This image was taken at an angle: 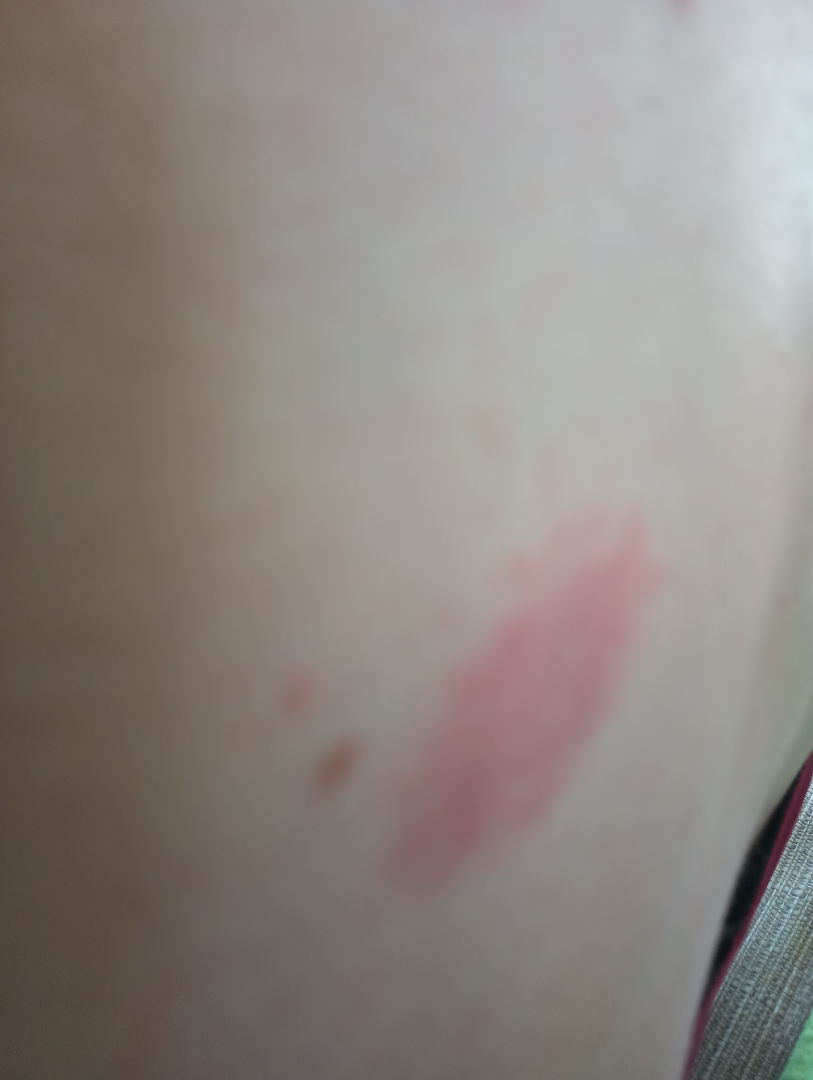<summary>
<assessment>unable to determine</assessment>
</summary>